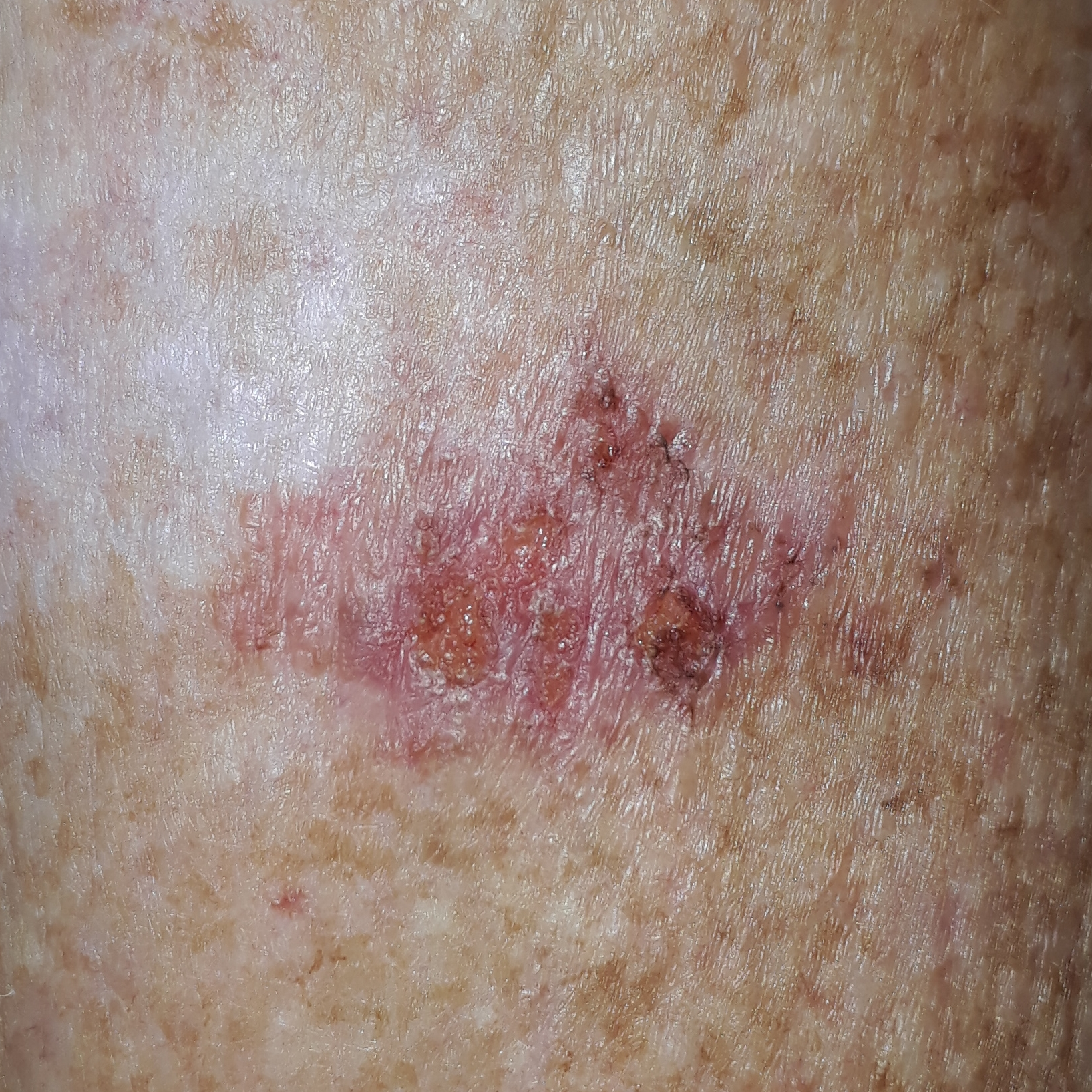Q: What is the imaging modality?
A: smartphone clinical photo
Q: What is the patient's skin type?
A: II
Q: Tell me about the patient.
A: male, 64 years old
Q: What are the lesion's dimensions?
A: 30 × 20 mm
Q: What symptoms does the patient report?
A: pain, bleeding, itching, elevation, growth
Q: What is the diagnosis?
A: basal cell carcinoma (biopsy-proven)